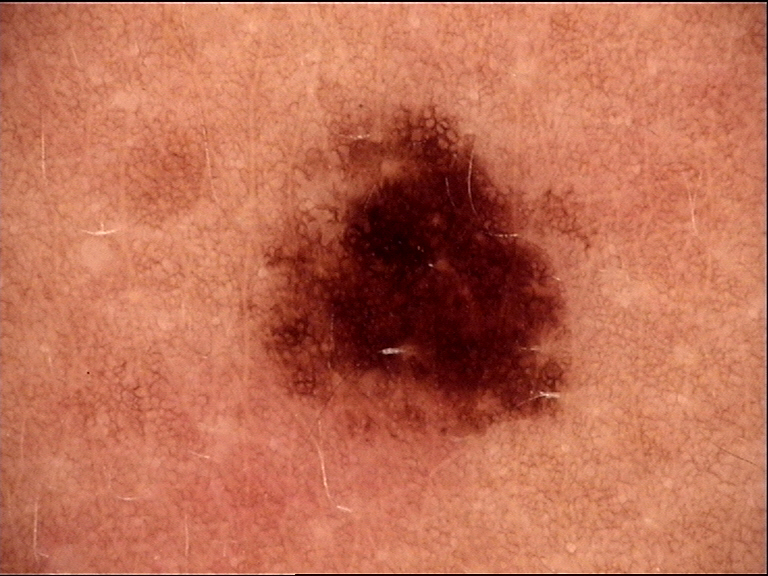A dermoscopic photograph of a skin lesion. The diagnosis was a dysplastic junctional nevus.